Located on the top or side of the foot. The photograph is a close-up of the affected area. The contributor is a female aged 50–59:
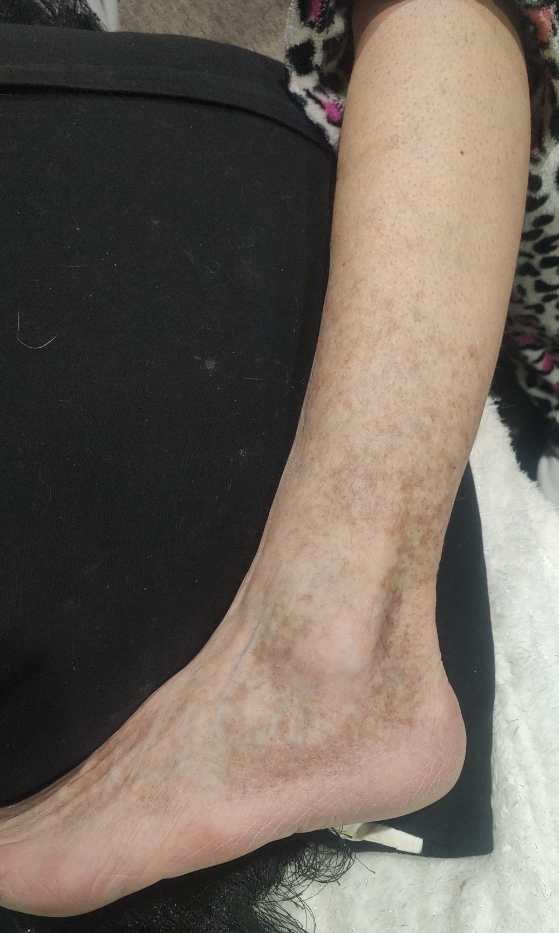lesion symptoms = bothersome appearance, surface texture = flat, patient describes the issue as = a pigmentary problem, assessment = Hemosiderin pigmentation of skin due to venous insufficiency (weight 1.00).